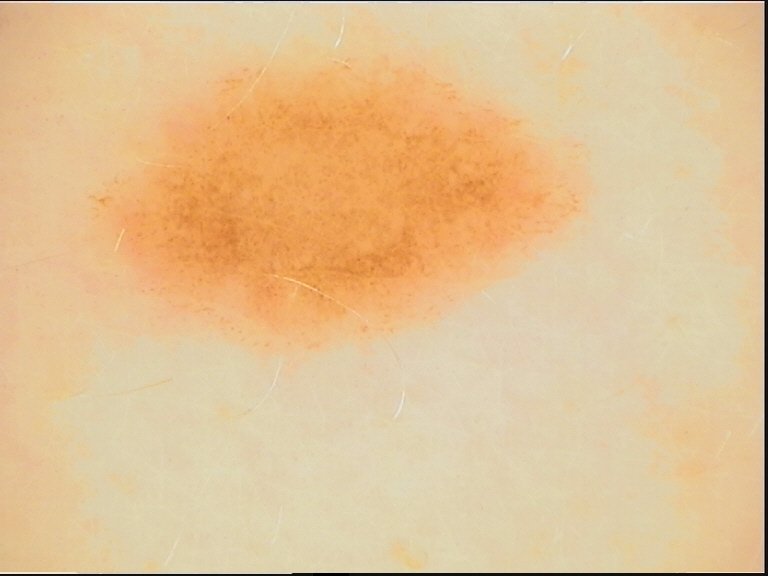A dermatoscopic image of a skin lesion.
The morphology is that of a banal lesion.
Classified as a junctional nevus.